A dermoscopic close-up of a skin lesion.
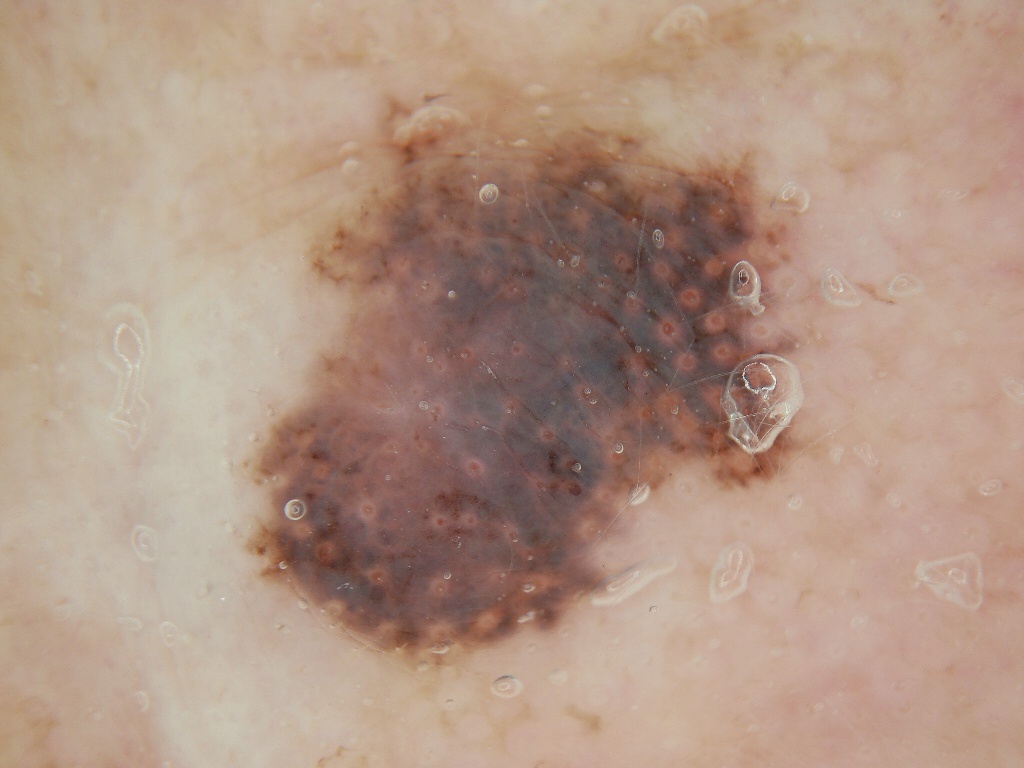Dermoscopic examination shows no globules, streaks, pigment network, negative network, or milia-like cysts.
As (left, top, right, bottom), lesion location: <bbox>215, 77, 899, 696</bbox>.
The lesion takes up a large portion of the image.
Diagnosed as a melanocytic nevus, a benign skin lesion.